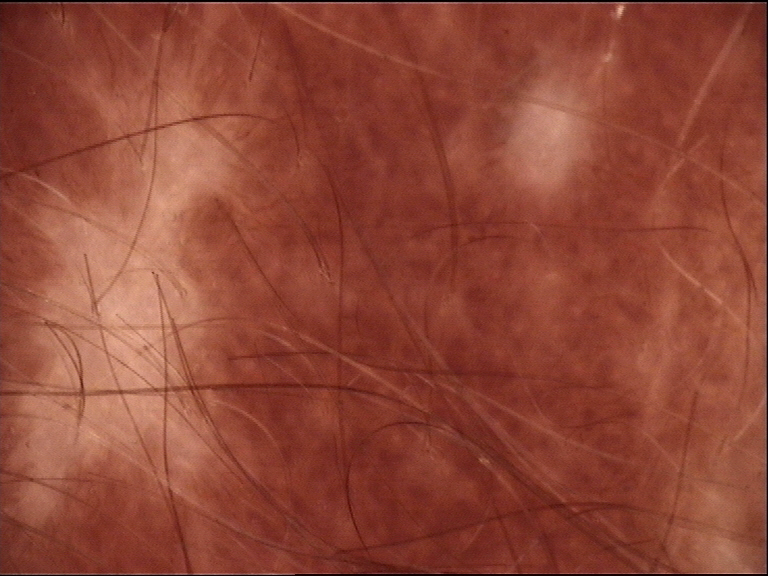A dermoscopy image of a single skin lesion.
The morphology is that of a banal lesion.
Classified as a congenital junctional nevus.